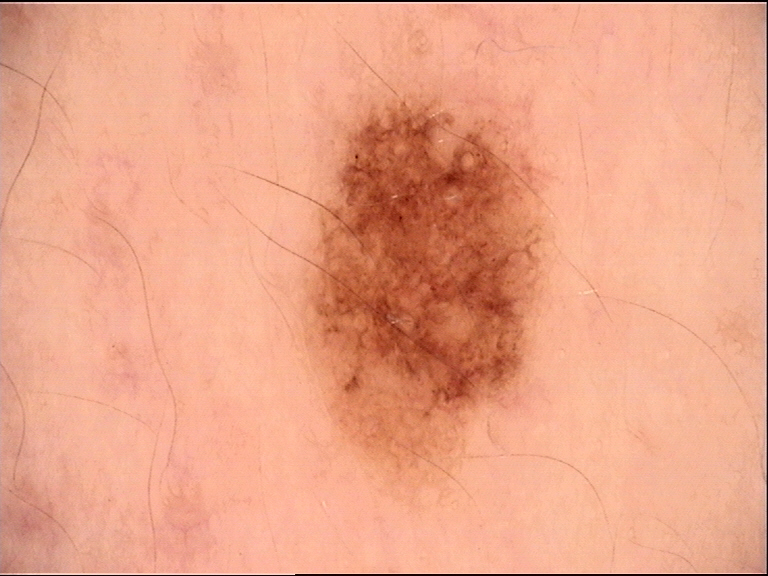A dermatoscopic image of a skin lesion. Diagnosed as a benign lesion — a dysplastic junctional nevus.